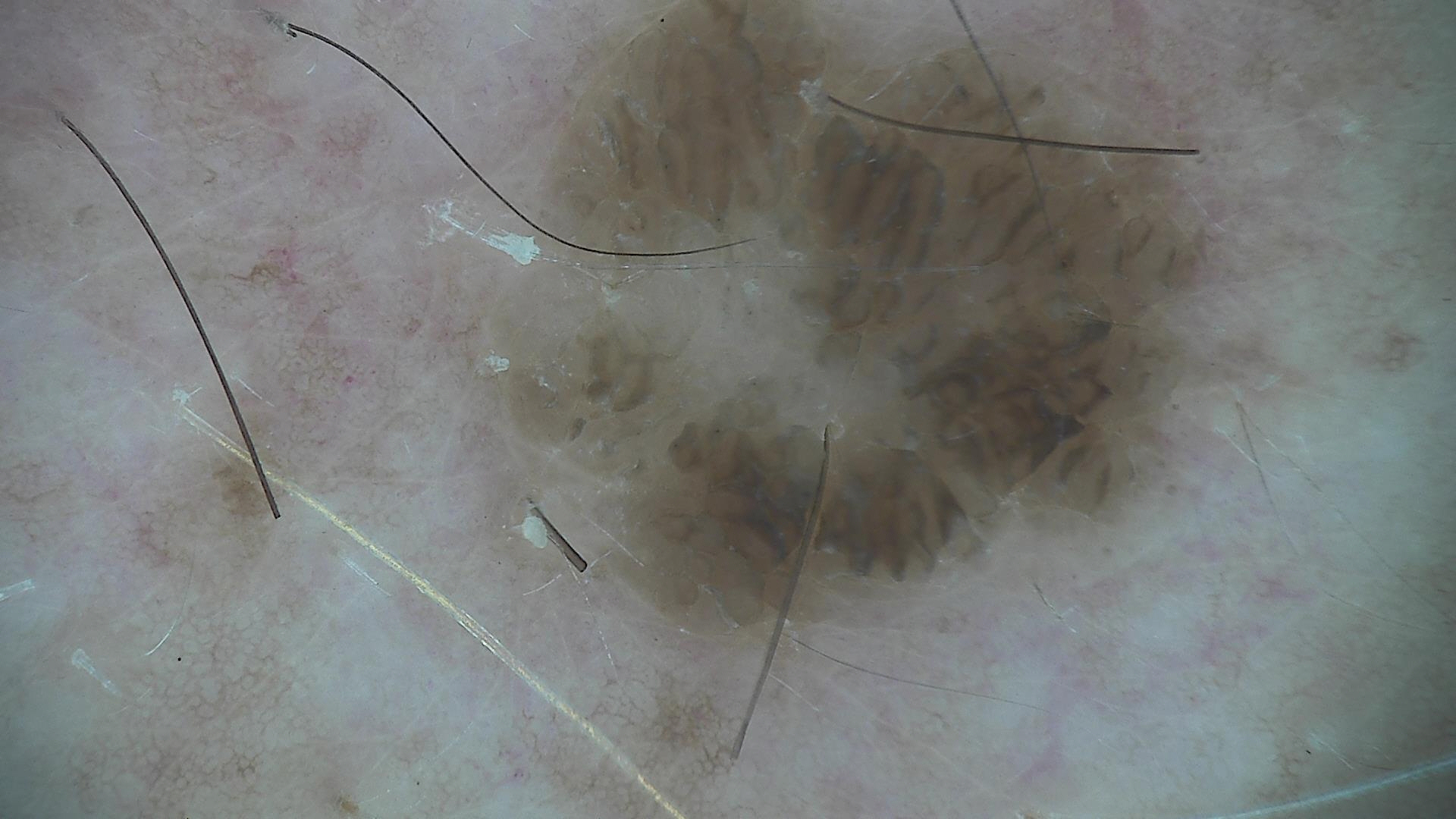<dermoscopy>
<image>dermatoscopy</image>
<lesion_type>
<main_class>keratinocytic</main_class>
</lesion_type>
<diagnosis>
<name>seborrheic keratosis</name>
<code>sk</code>
<malignancy>benign</malignancy>
<super_class>non-melanocytic</super_class>
<confirmation>expert consensus</confirmation>
</diagnosis>
</dermoscopy>